Dermoscopy of a skin lesion.
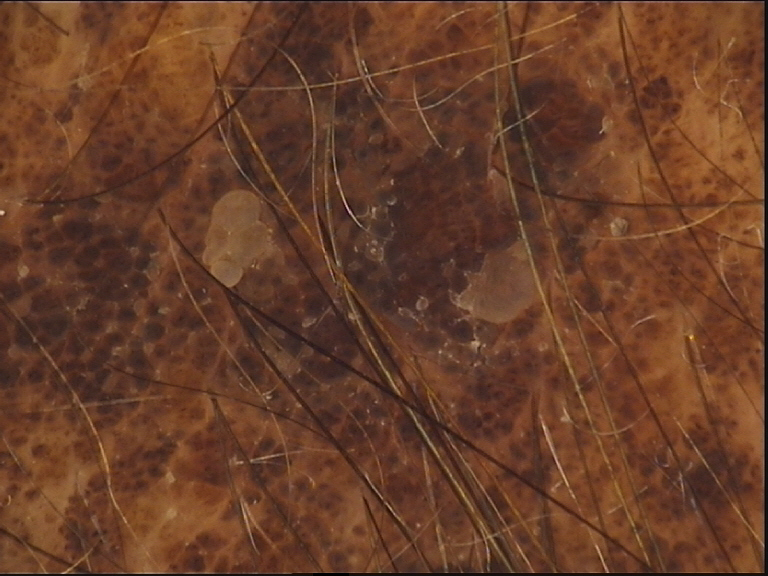Findings:
* lesion type · banal
* diagnosis · congenital compound nevus (expert consensus)